The patient is female. The lesion involves the arm and leg. The photo was captured at a distance.
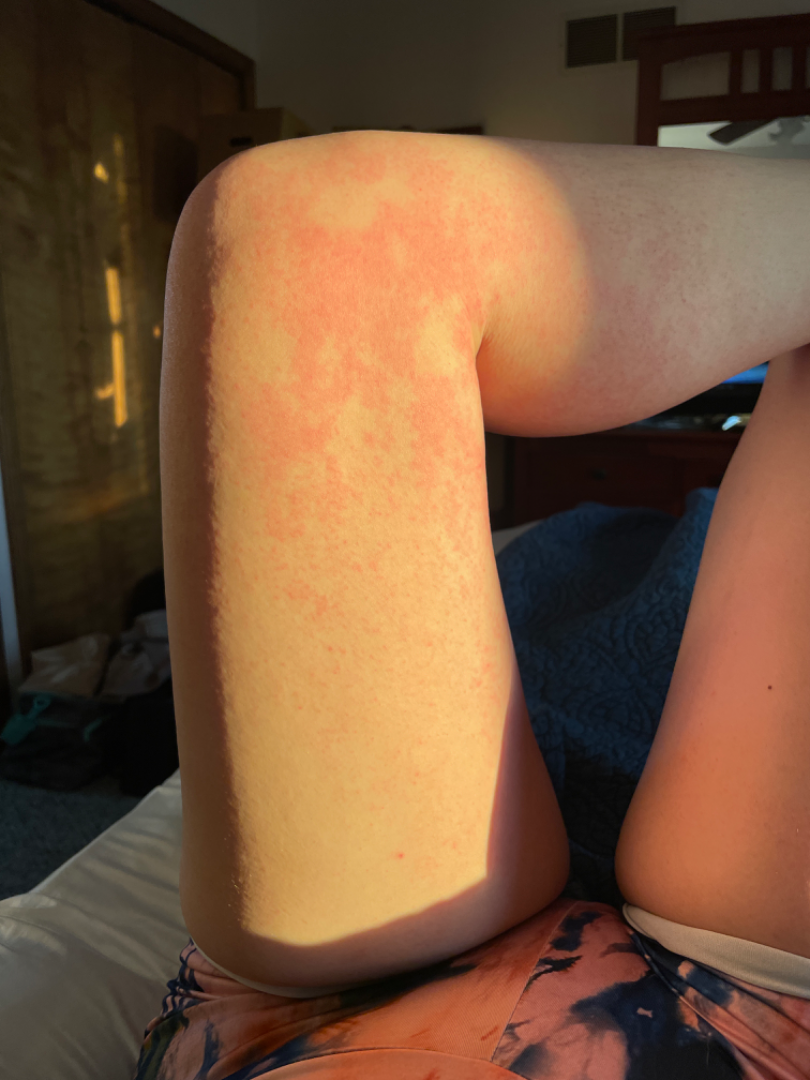impression = the leading consideration is Eczema; possibly Drug Rash; also raised was Urticaria